A skin lesion imaged with contact-polarized dermoscopy · per the chart, a first-degree relative with melanoma but no previous melanoma · a female subject roughly 20 years of age · recorded as Fitzpatrick phototype III: 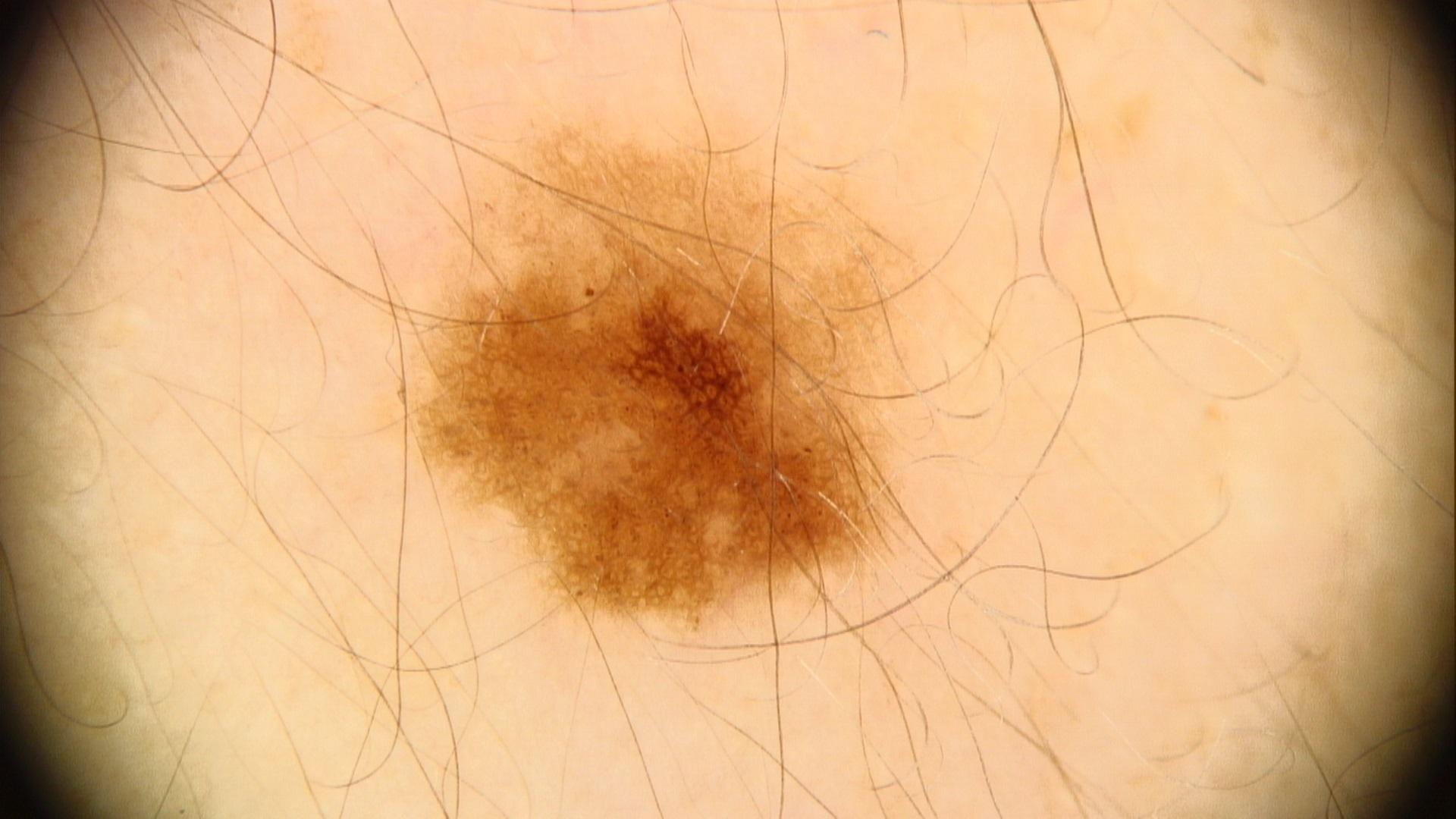{
  "lesion_location": {
    "region": "the trunk",
    "detail": "the posterior trunk"
  },
  "diagnosis": {
    "name": "Nevus",
    "malignancy": "benign",
    "confirmation": "expert clinical impression",
    "lineage": "melanocytic"
  }
}